A skin lesion imaged with a dermatoscope; a female subject 47 years of age.
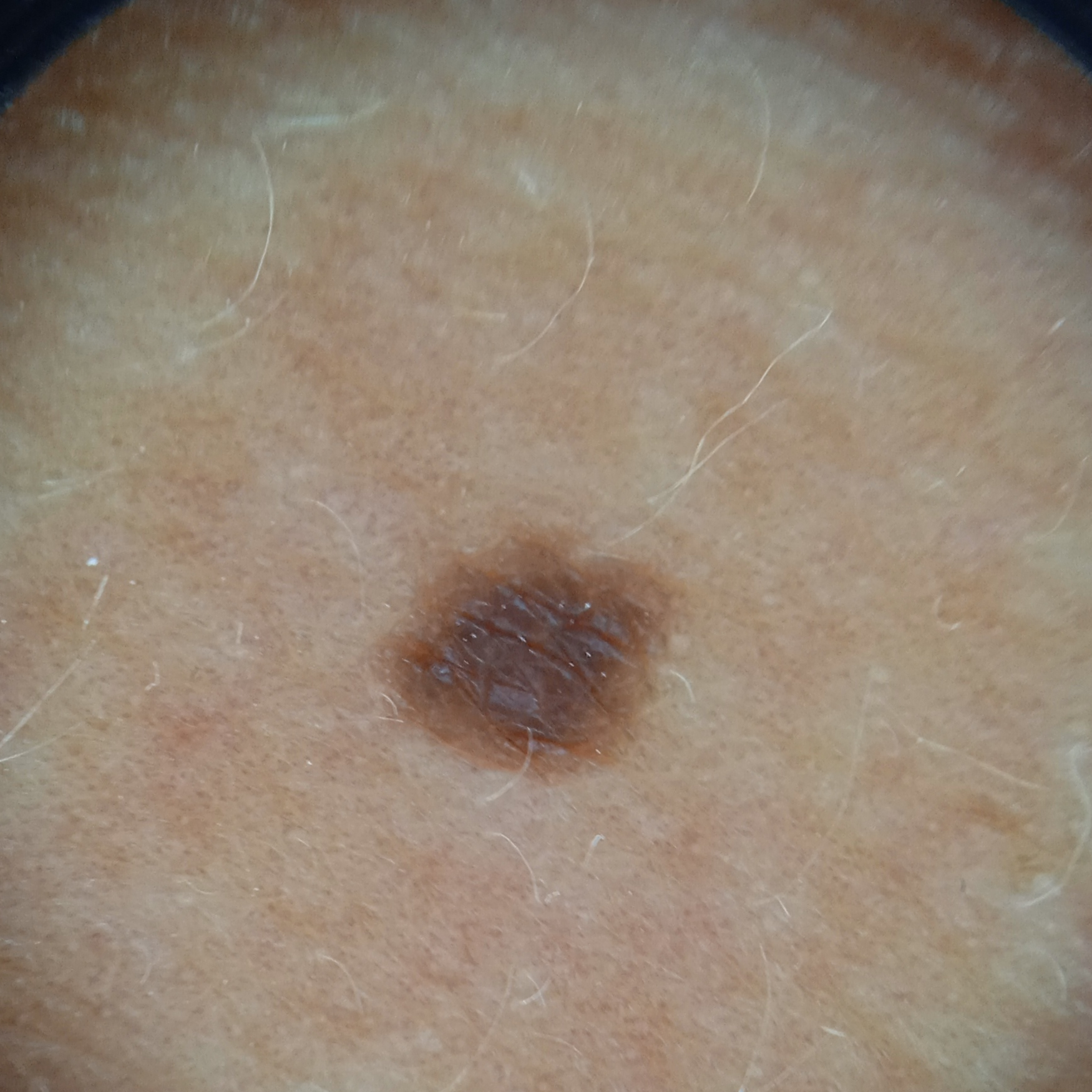The lesion involves an arm.
Measuring roughly 3.3 mm.
The dermatologists' assessment was a melanocytic nevus.